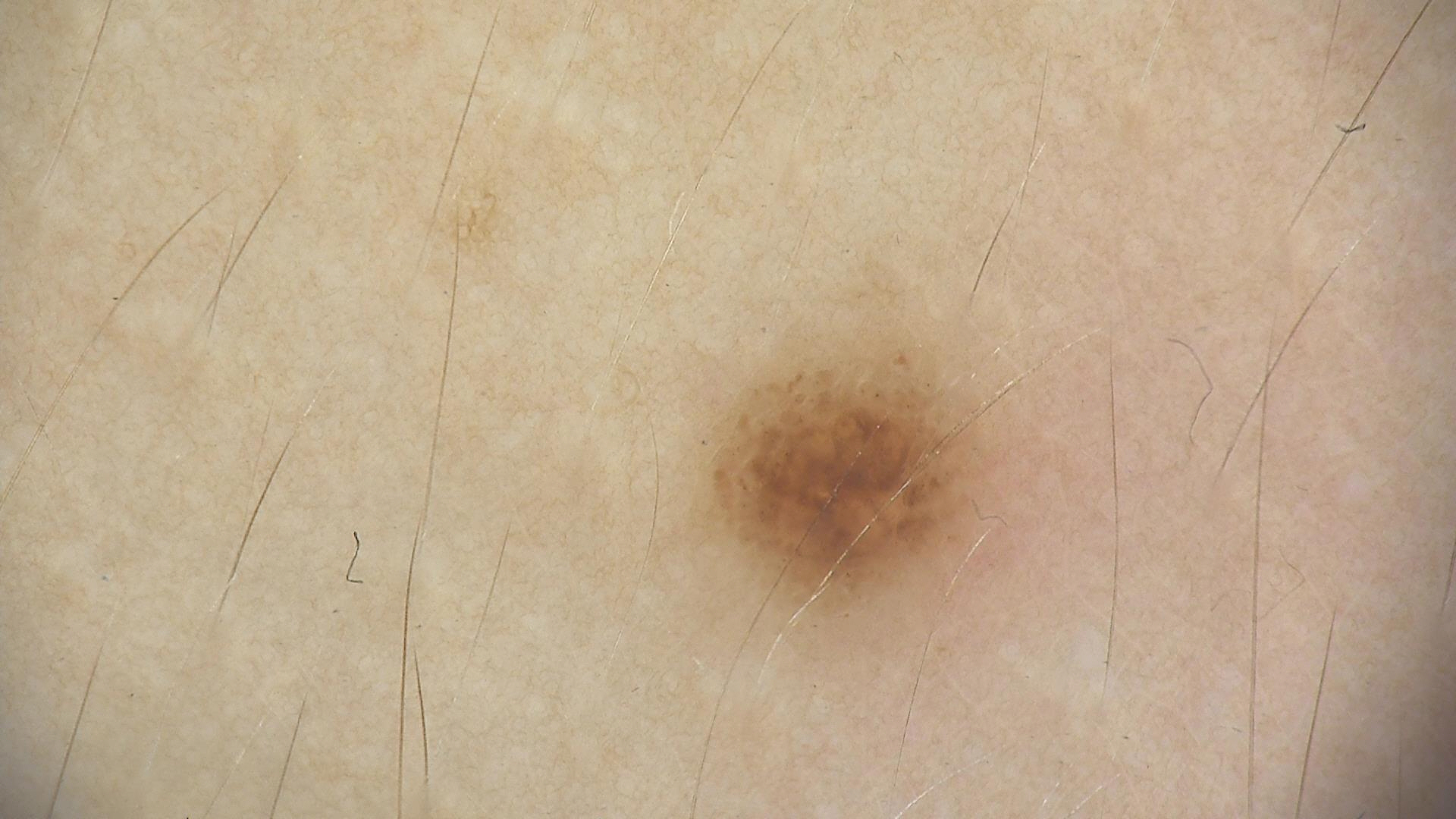Findings: A dermoscopy image of a single skin lesion. Impression: Labeled as a dysplastic junctional nevus.